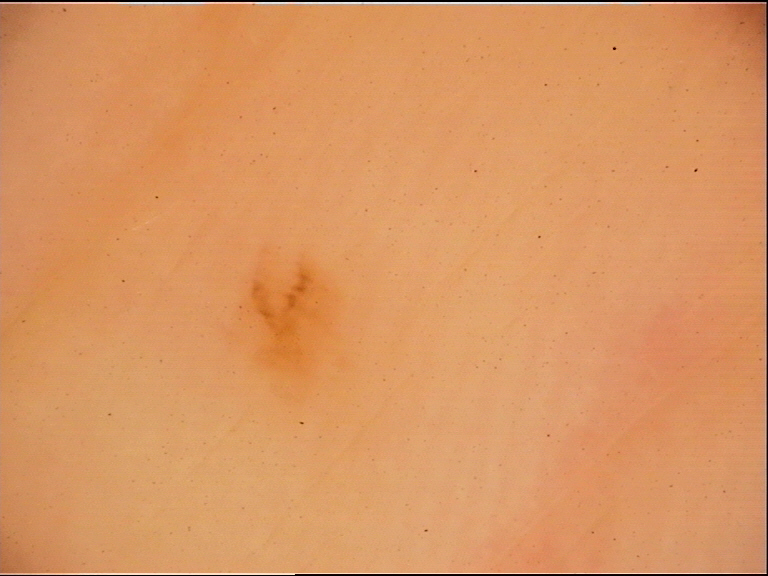image: dermatoscopy
lesion_type:
  main_class: banal
  pattern: junctional
diagnosis:
  name: acral junctional nevus
  code: ajb
  malignancy: benign
  super_class: melanocytic
  confirmation: expert consensus